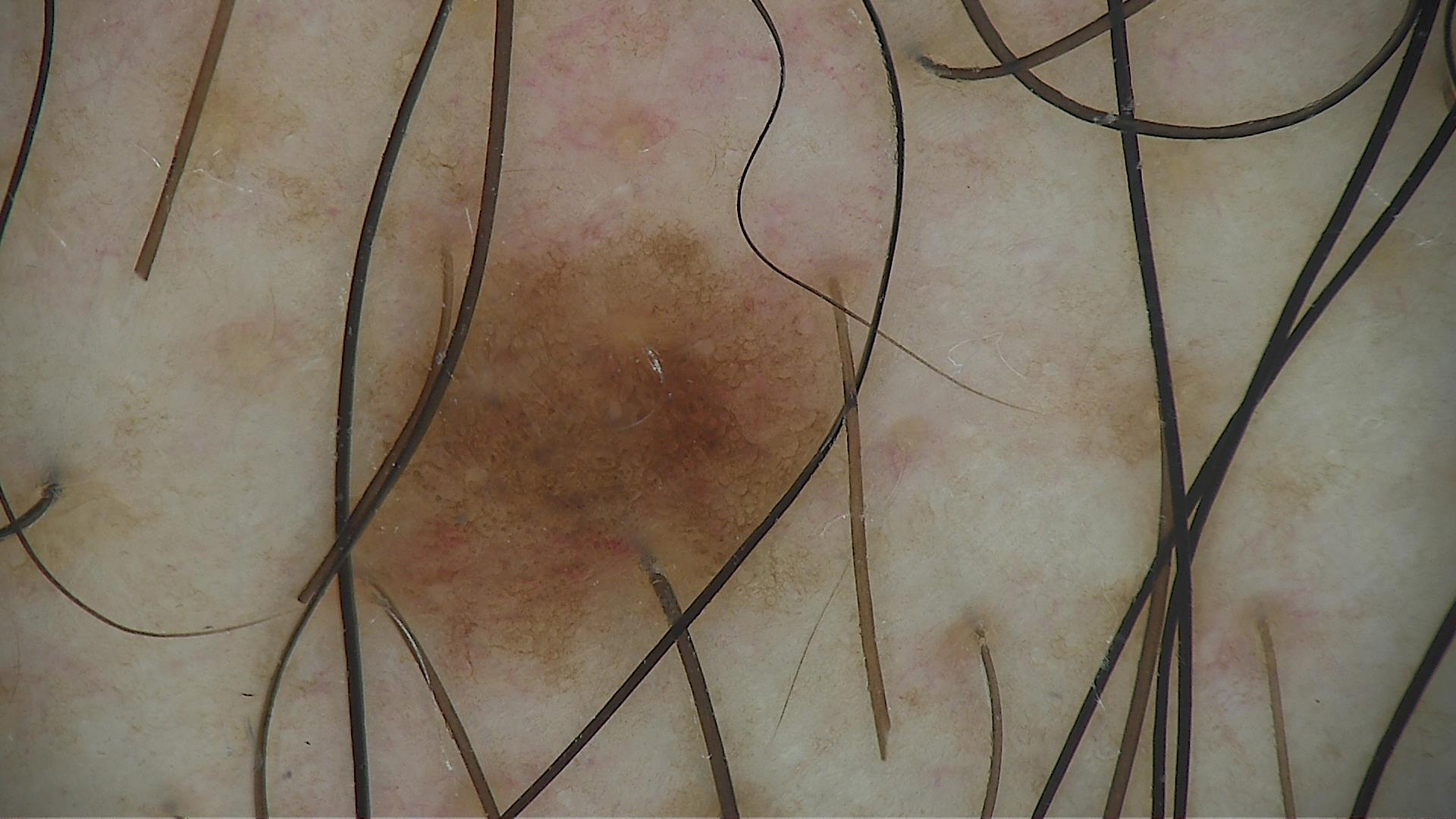Diagnosed as a dysplastic junctional nevus.